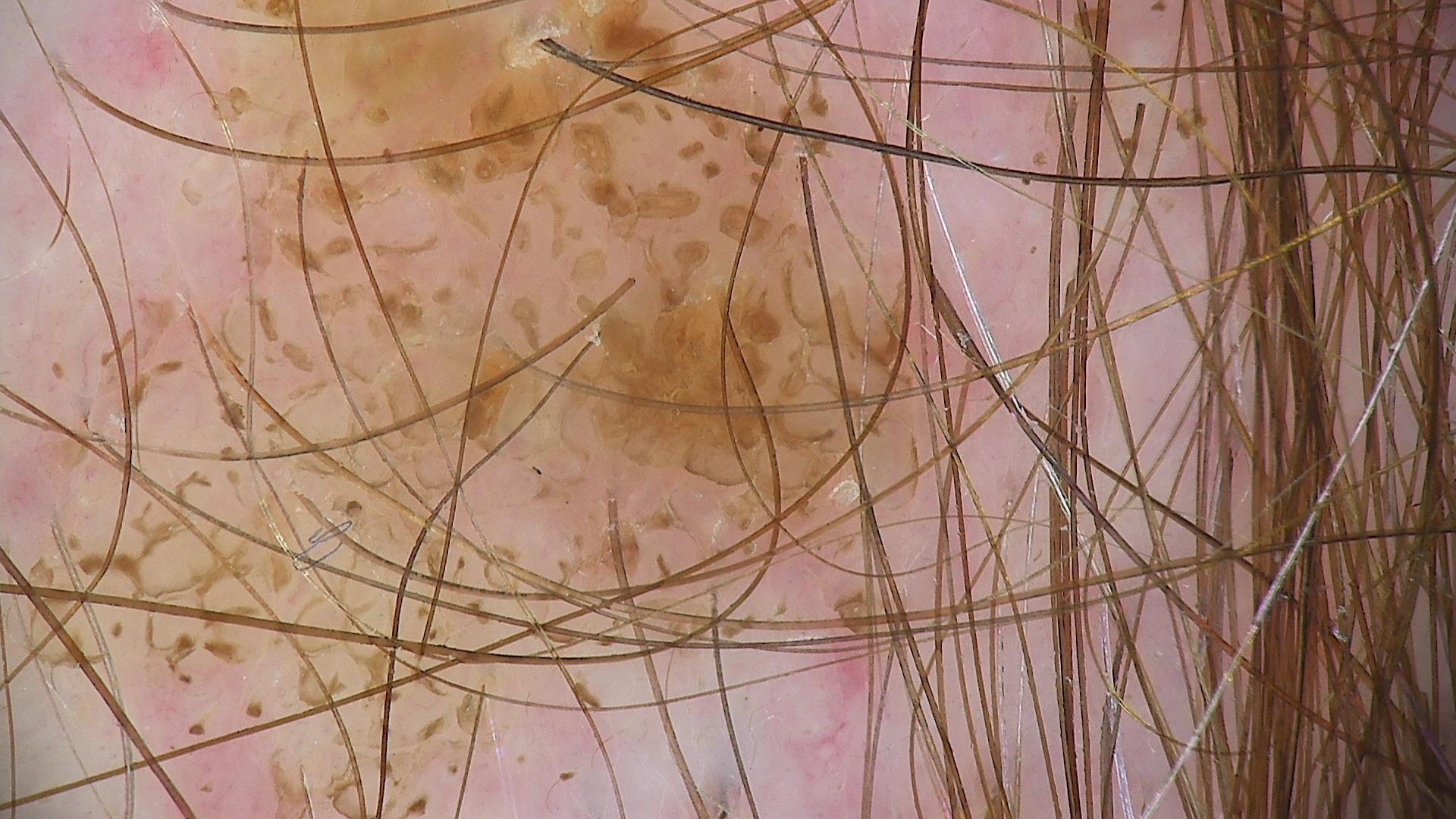The diagnosis was a compound nevus.